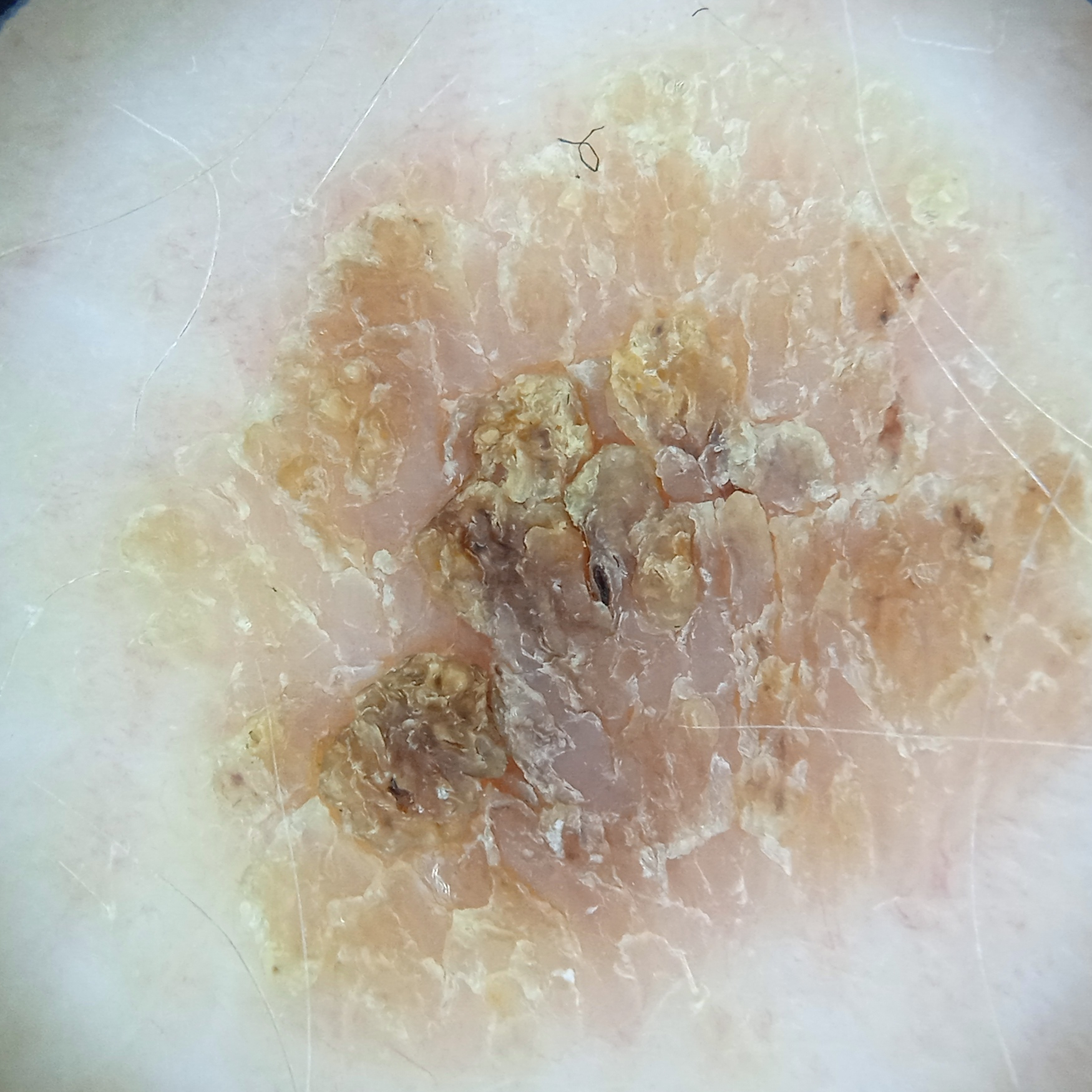{
  "referral": "research study (no referral diagnosis)",
  "sun_reaction": "skin reddens with sun exposure",
  "risk_factors": {
    "positive": [
      "a personal history of cancer"
    ]
  },
  "mole_burden": "few melanocytic nevi overall",
  "image": "dermoscopic image",
  "lesion_location": "the back",
  "lesion_size": {
    "diameter_mm": 11.0
  },
  "diagnosis": {
    "name": "seborrheic keratosis",
    "malignancy": "benign"
  }
}